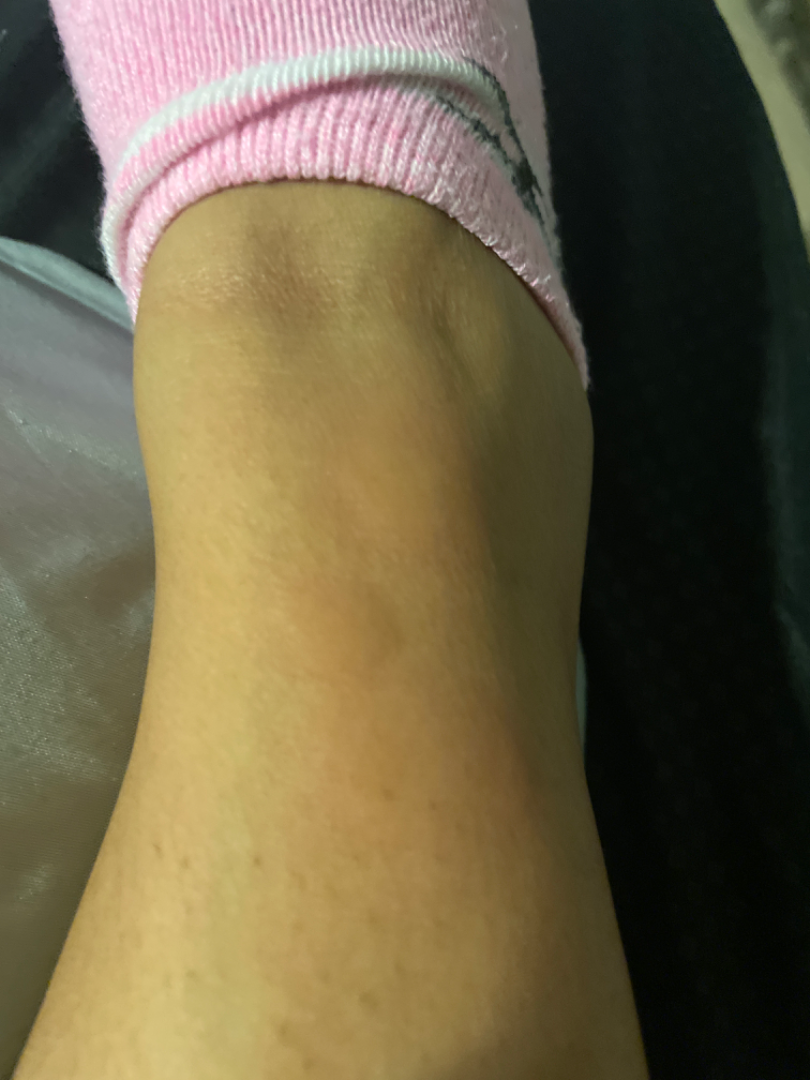Q: Could the case be diagnosed?
A: indeterminate